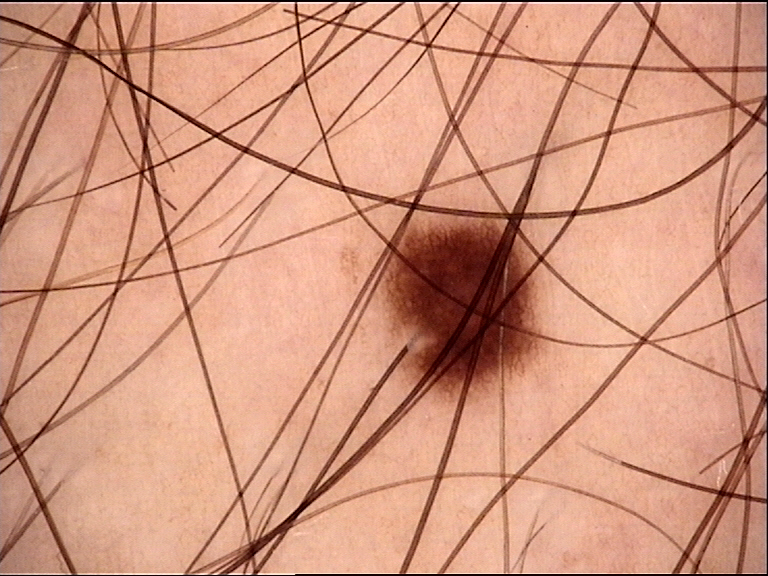<lesion>
<diagnosis>
<name>dysplastic junctional nevus</name>
<code>jd</code>
<malignancy>benign</malignancy>
<super_class>melanocytic</super_class>
<confirmation>expert consensus</confirmation>
</diagnosis>
</lesion>